A skin lesion imaged with a dermatoscope:
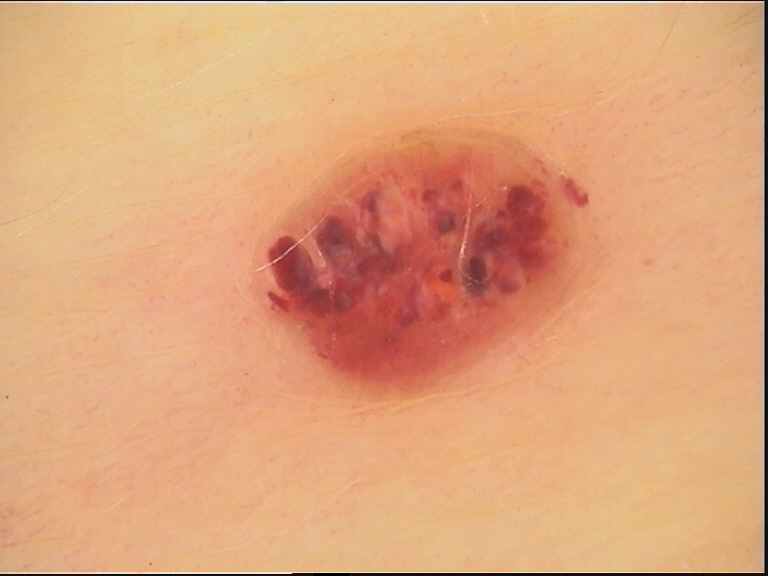Q: What kind of lesion is this?
A: vascular
Q: What is the diagnosis?
A: hemangioma (expert consensus)